This is a close-up image — 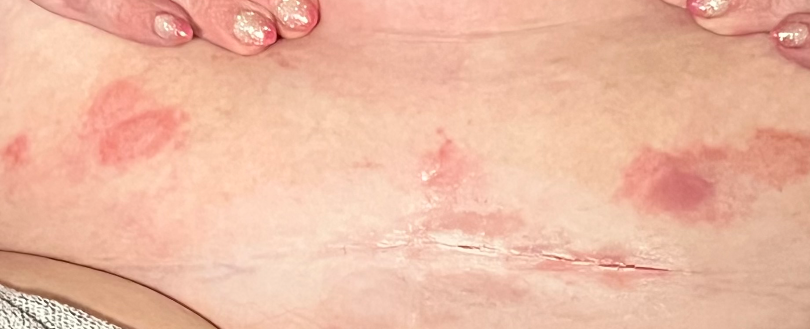On dermatologist assessment of the image: the differential, in no particular order, includes Pityriasis rosea, Psoriasis and Hypersensitivity.